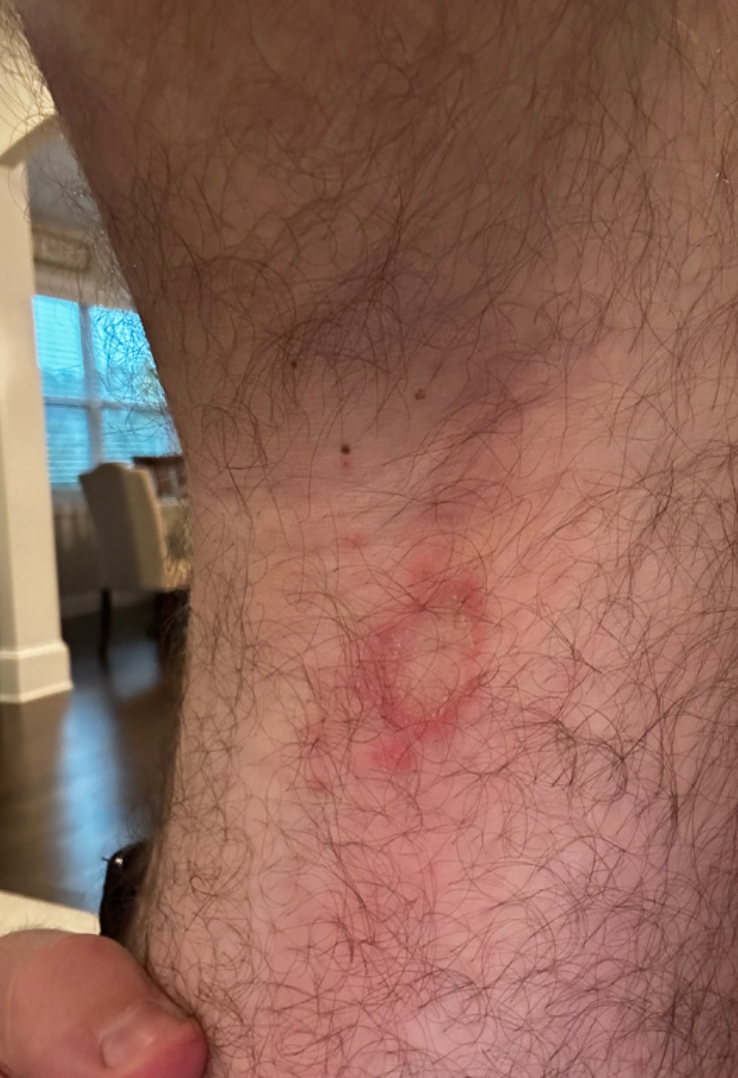The skin findings could not be characterized from the image. No constitutional symptoms were reported. A close-up photograph. The patient described the issue as a rash. The contributor is a male aged 30–39. The leg is involved. The patient reports the condition has been present for one to four weeks. The lesion is described as raised or bumpy and rough or flaky.